A dermoscopic close-up of a skin lesion.
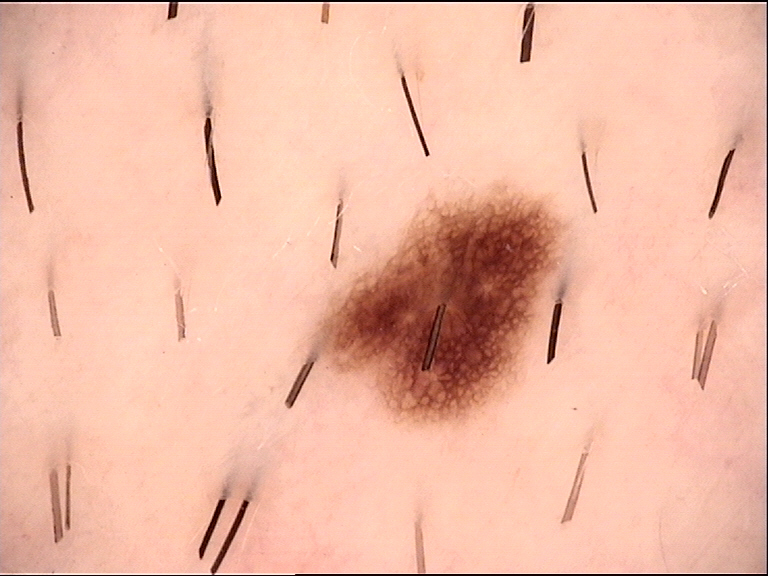Conclusion:
Labeled as a benign lesion — a dysplastic junctional nevus.